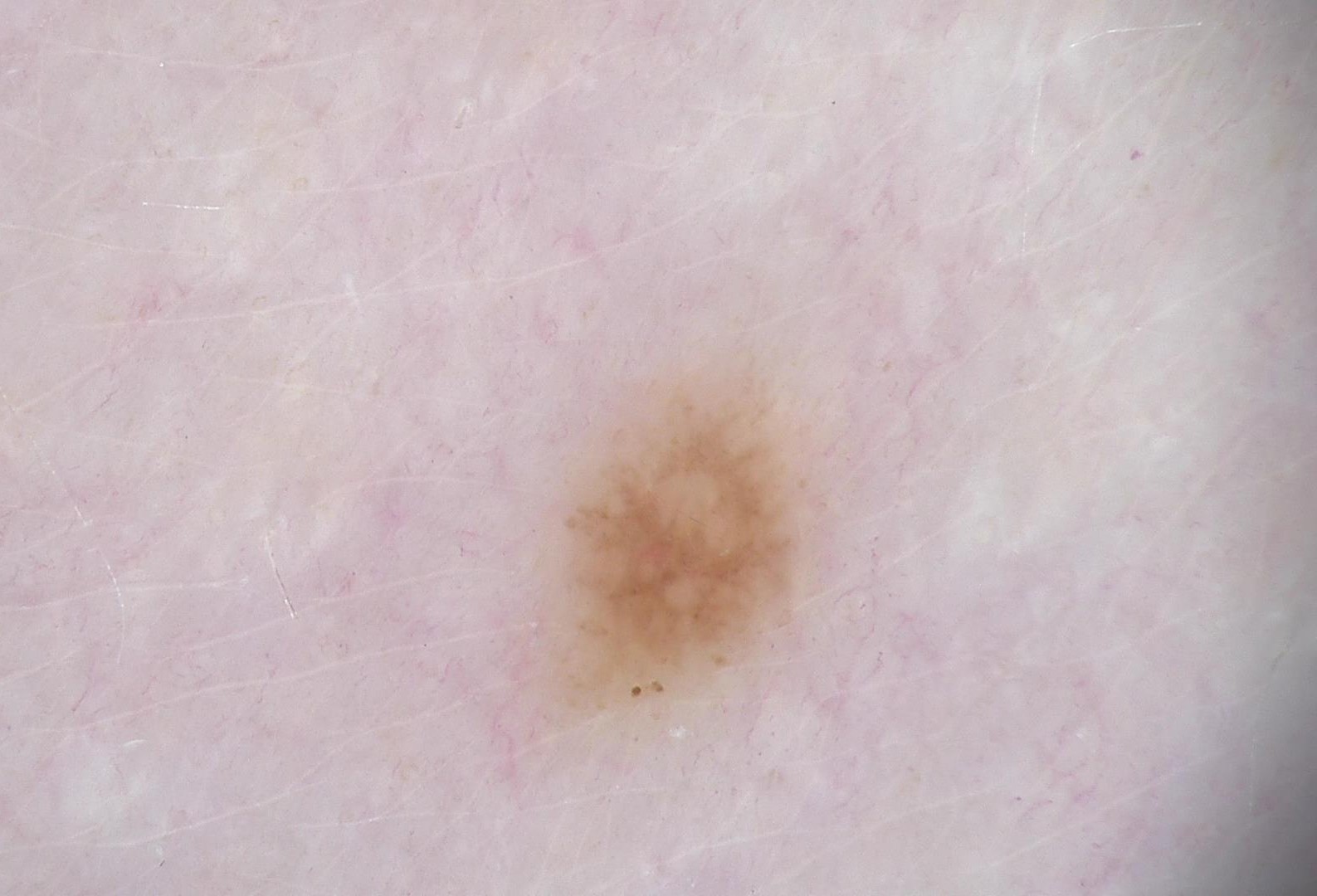<case>
<image>dermatoscopy</image>
<diagnosis>
<name>dysplastic junctional nevus</name>
<code>jd</code>
<malignancy>benign</malignancy>
<super_class>melanocytic</super_class>
<confirmation>expert consensus</confirmation>
</diagnosis>
</case>